A dermatoscopic image of a skin lesion; the patient describes having a moderate number of moles; referred with a clinical suspicion of melanocytic nevus; by self-report, no family history of skin cancer and no immunosuppression; the patient says their skin reddens with sun exposure; a female subject 59 years old.
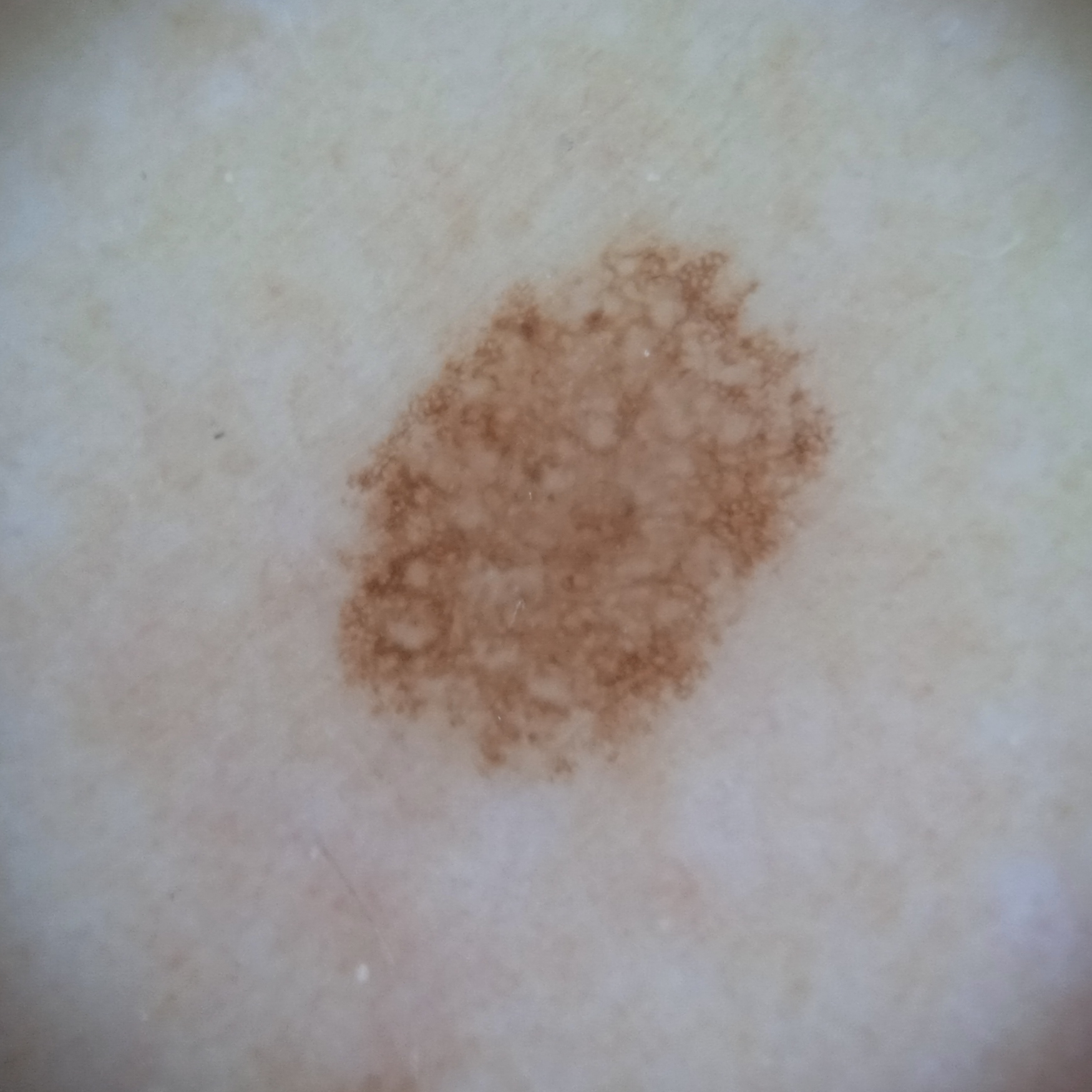Summary:
The lesion is on an arm. Measuring roughly 6.7 mm.
Conclusion:
The biopsy diagnosis was an atypical (dysplastic) nevus, following excision.